FST III · a female subject about 85 years old or older · a clinical overview photograph of a skin lesion:
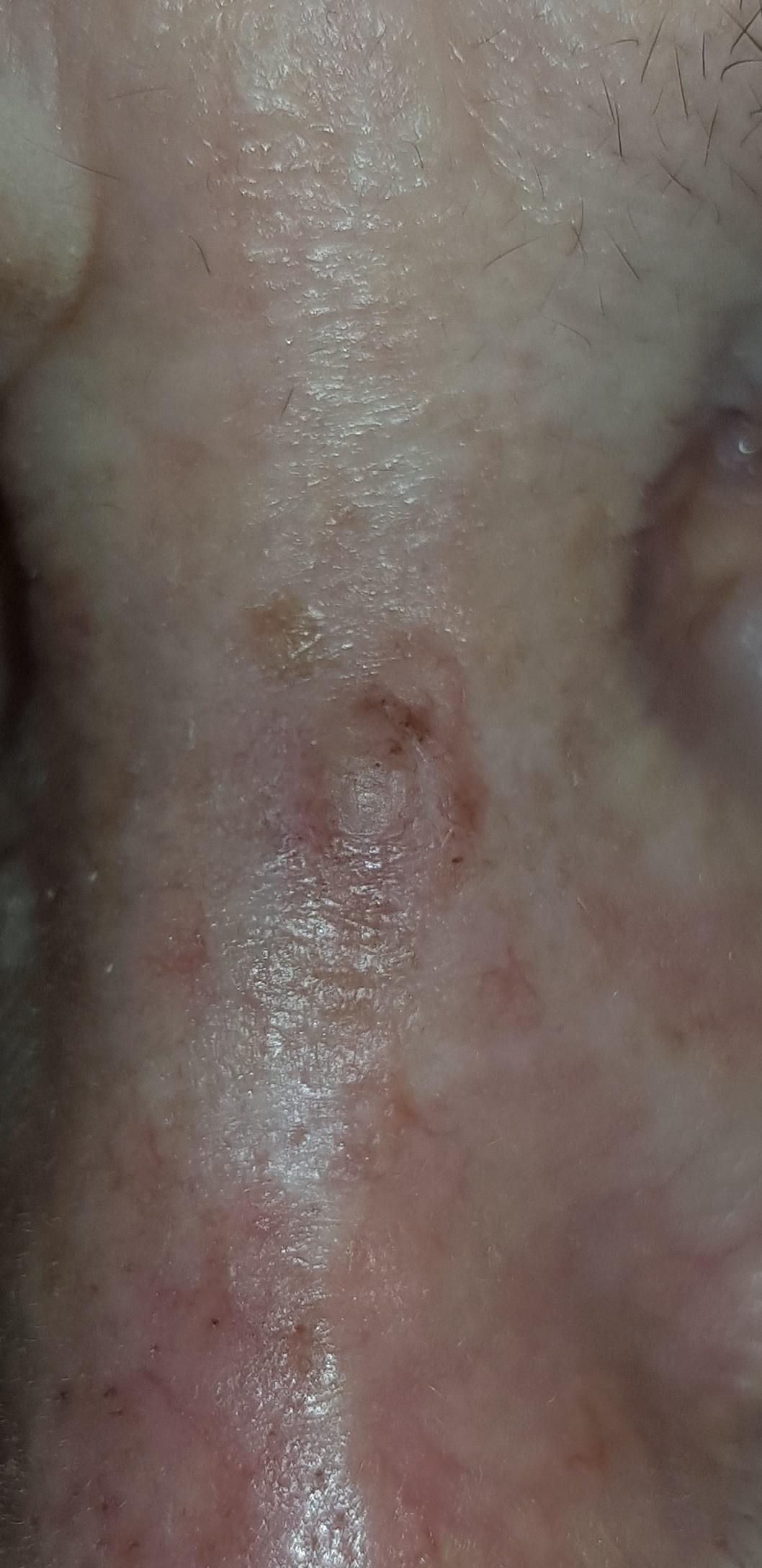anatomic site=the head or neck | diagnosis=Basal cell carcinoma (biopsy-proven).